Located on the arm · the photograph was taken at a distance · male contributor, age 30–39:
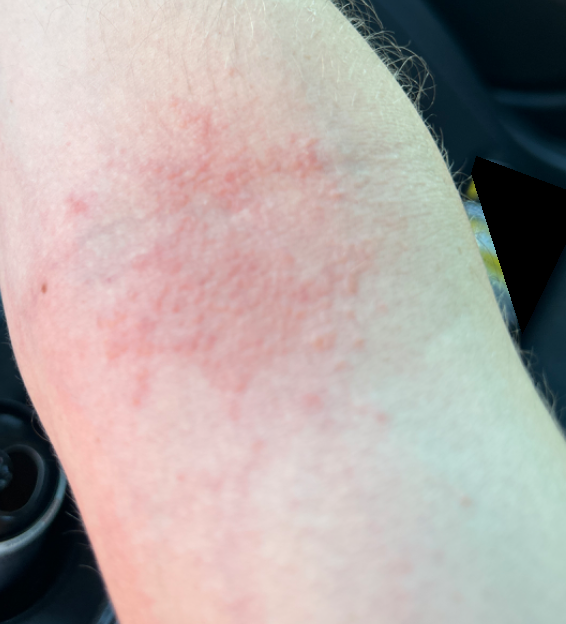Consistent with Eczema.